A dermoscopic photograph of a skin lesion: 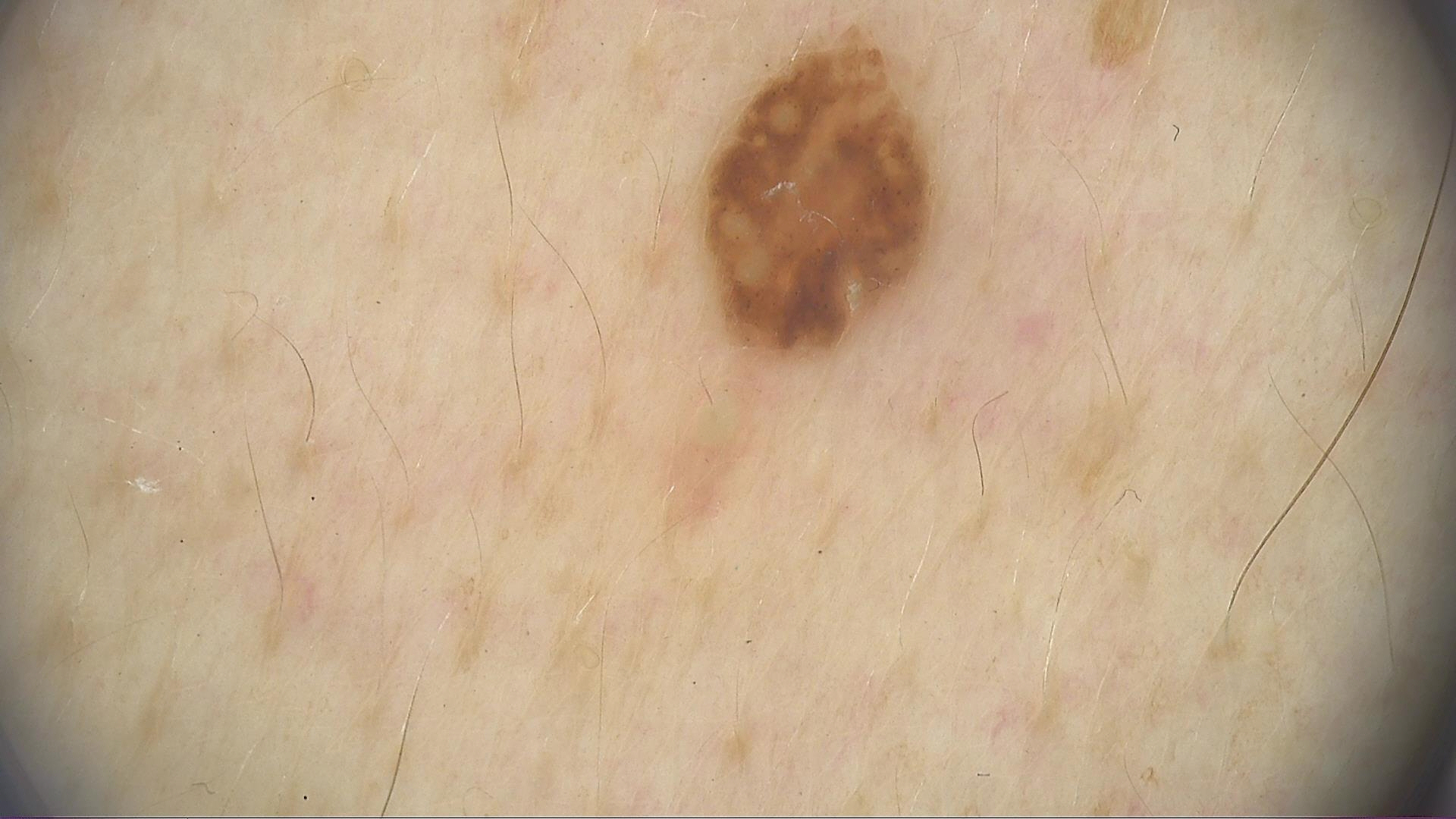Conclusion:
Diagnosed as a banal lesion — a compound nevus.